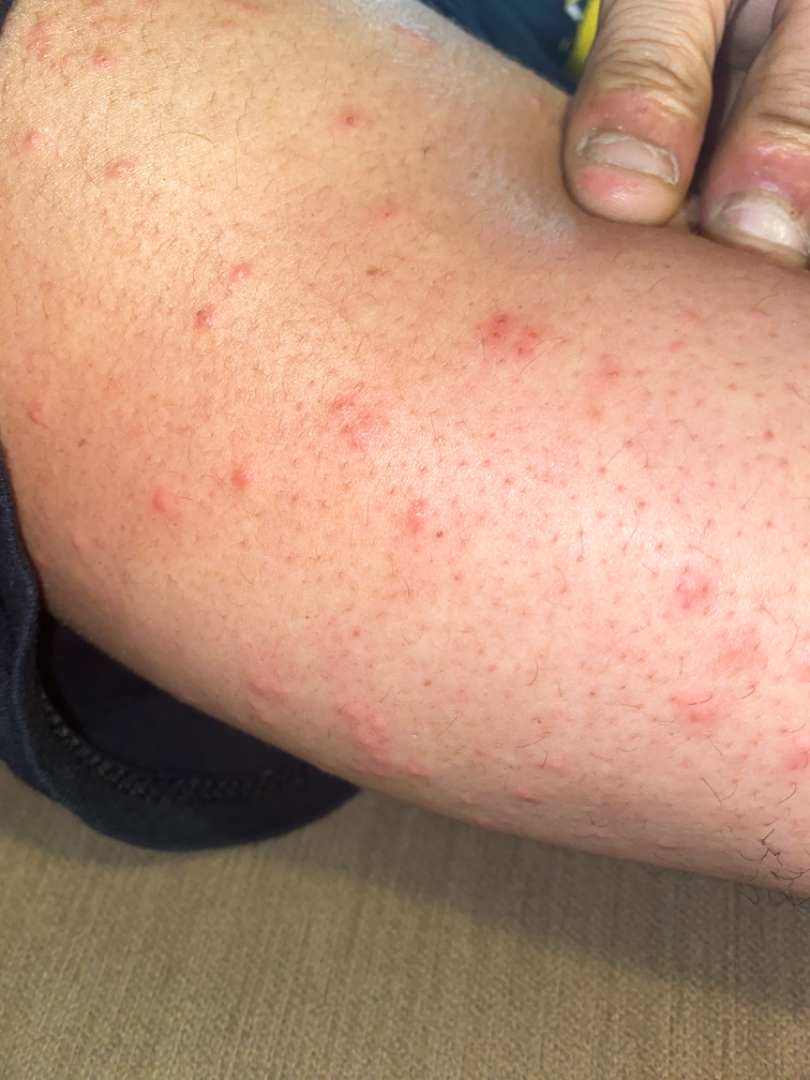assessment: could not be assessed.